The patient says their skin tans without first burning; the patient describes having numerous moles; imaged for a research study, with no referral diagnosis recorded.
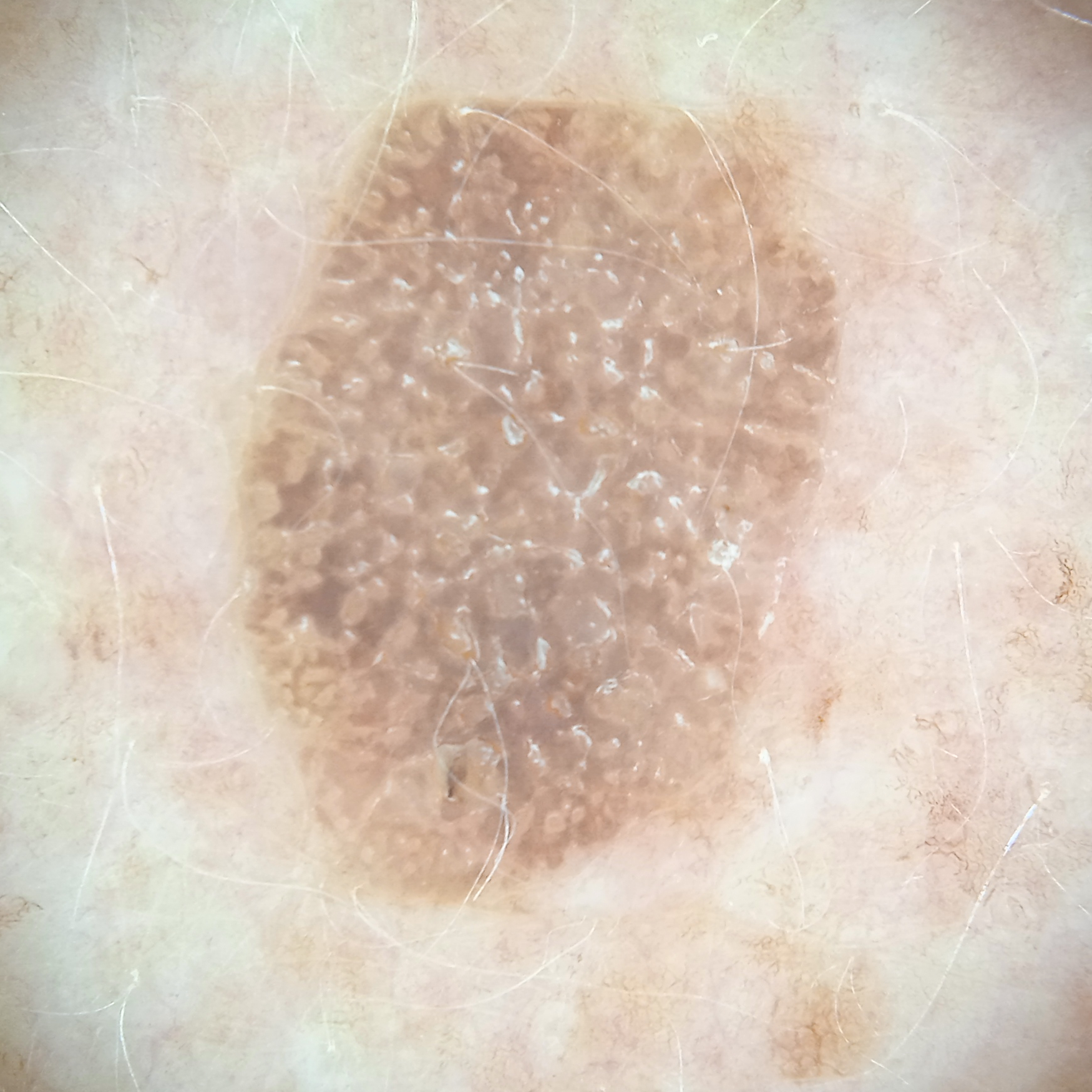location: the back | diameter: 9.6 mm | assessment: seborrheic keratosis (dermatologist consensus).